A dermoscopy image of a single skin lesion: 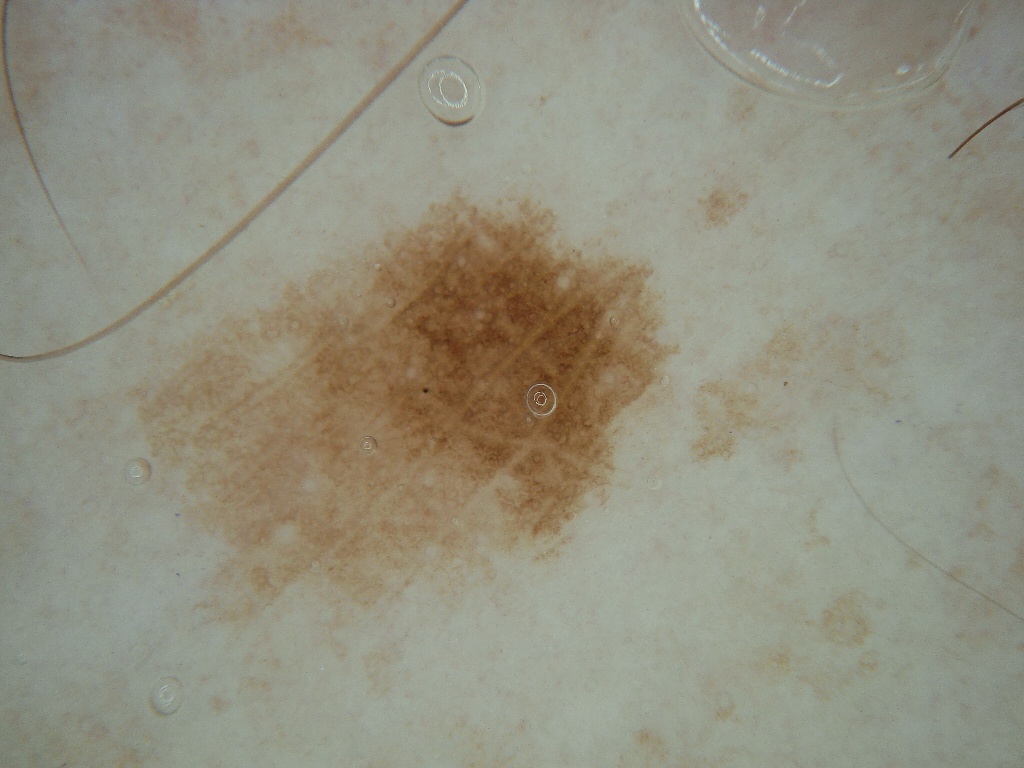With coordinates (x1, y1, x2, y2), the lesion is bounded by [122,194,668,619].
On dermoscopy, the lesion shows no globules or streaks.
The clinical diagnosis was a benign skin lesion.